A clinical close-up photograph of a skin lesion: 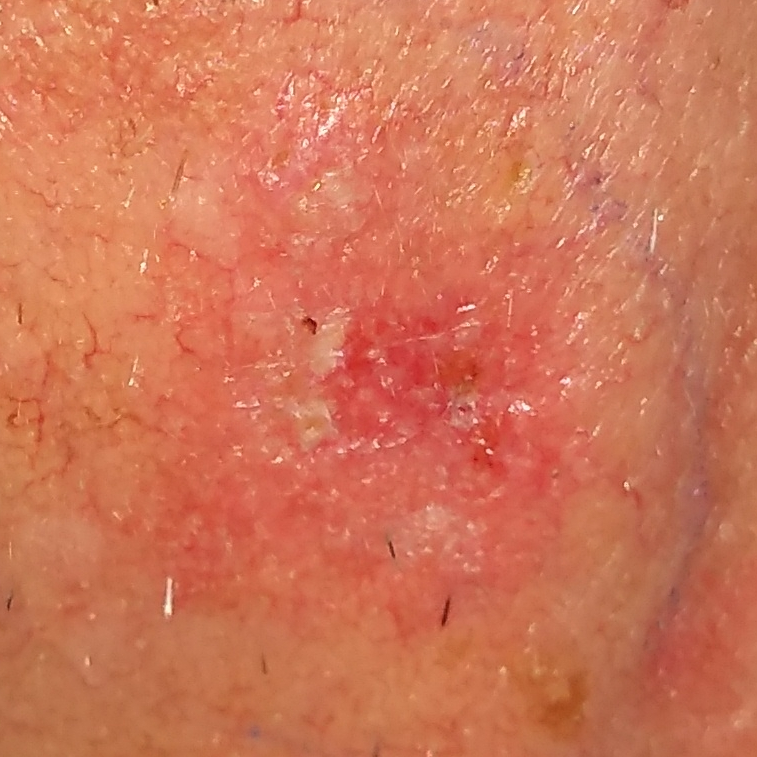The lesion involves the face. The patient reports that the lesion itches. Histopathologically confirmed as an actinic keratosis.